A skin lesion imaged with a dermatoscope.
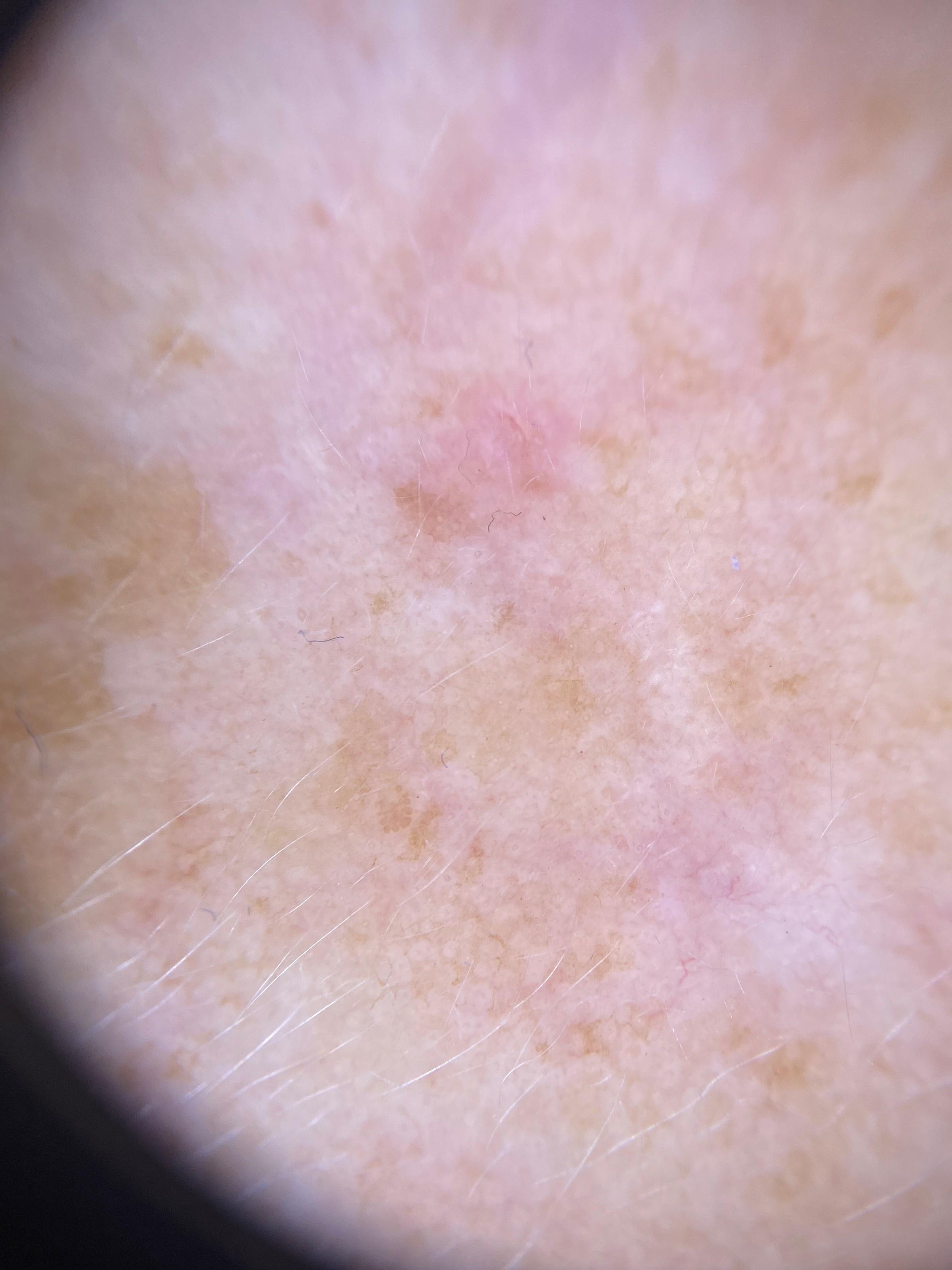Image and clinical context:
The lesion is located on the head or neck.
Diagnosis:
Confirmed on histopathology as a solar or actinic keratosis.